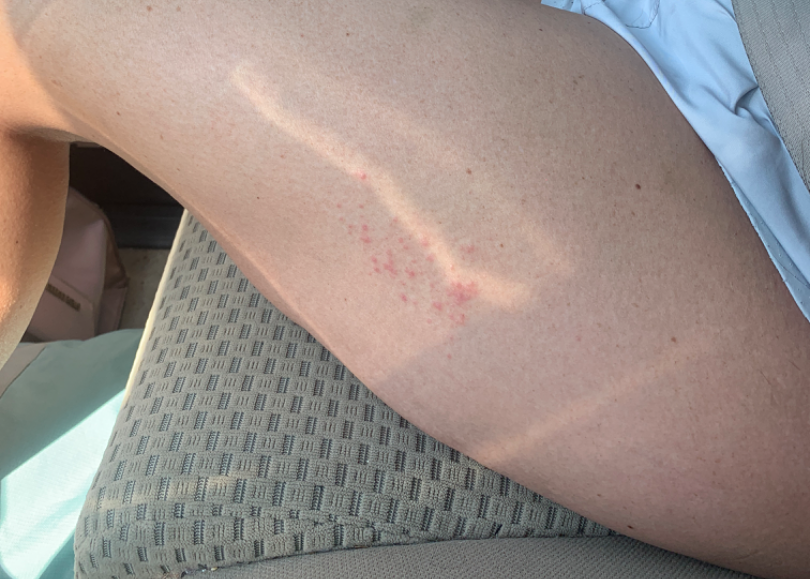No associated systemic symptoms reported.
Texture is reported as raised or bumpy.
Self-categorized by the patient as skin that appeared healthy to them.
The photograph was taken at a distance.
The patient notes the condition has been present for about one day.
Fitzpatrick skin type III.
The lesion involves the leg.
On remote dermatologist review: Folliculitis and Irritant Contact Dermatitis were each considered, in no particular order.